A dermoscopic image of a skin lesion; the subject is a male approximately 15 years of age: 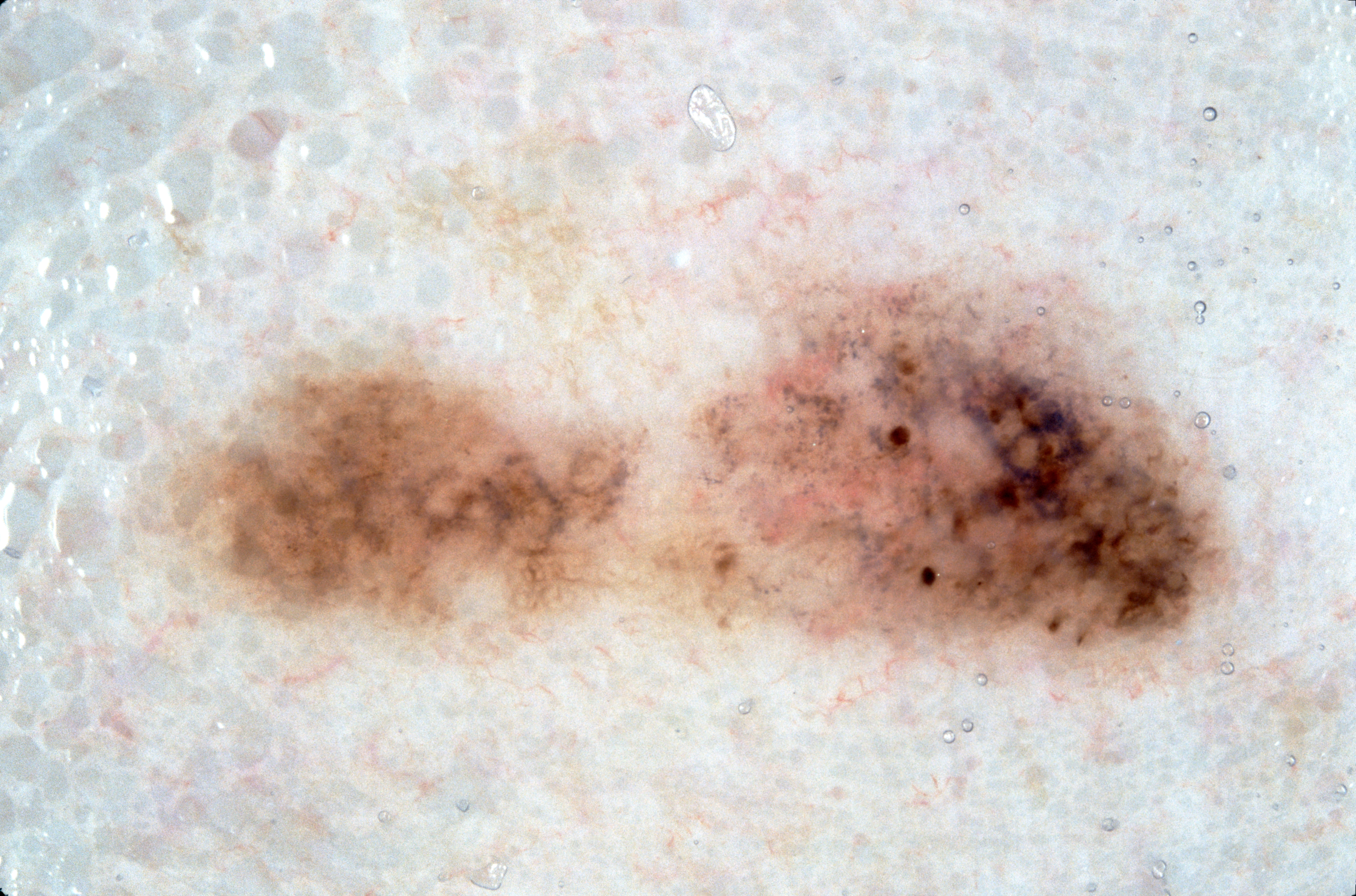Lesion location: x1=169 y1=227 x2=1267 y2=716. Dermoscopic review identifies milia-like cysts and pigment network; no negative network or streaks. Clinically diagnosed as a melanocytic nevus, a benign skin lesion.